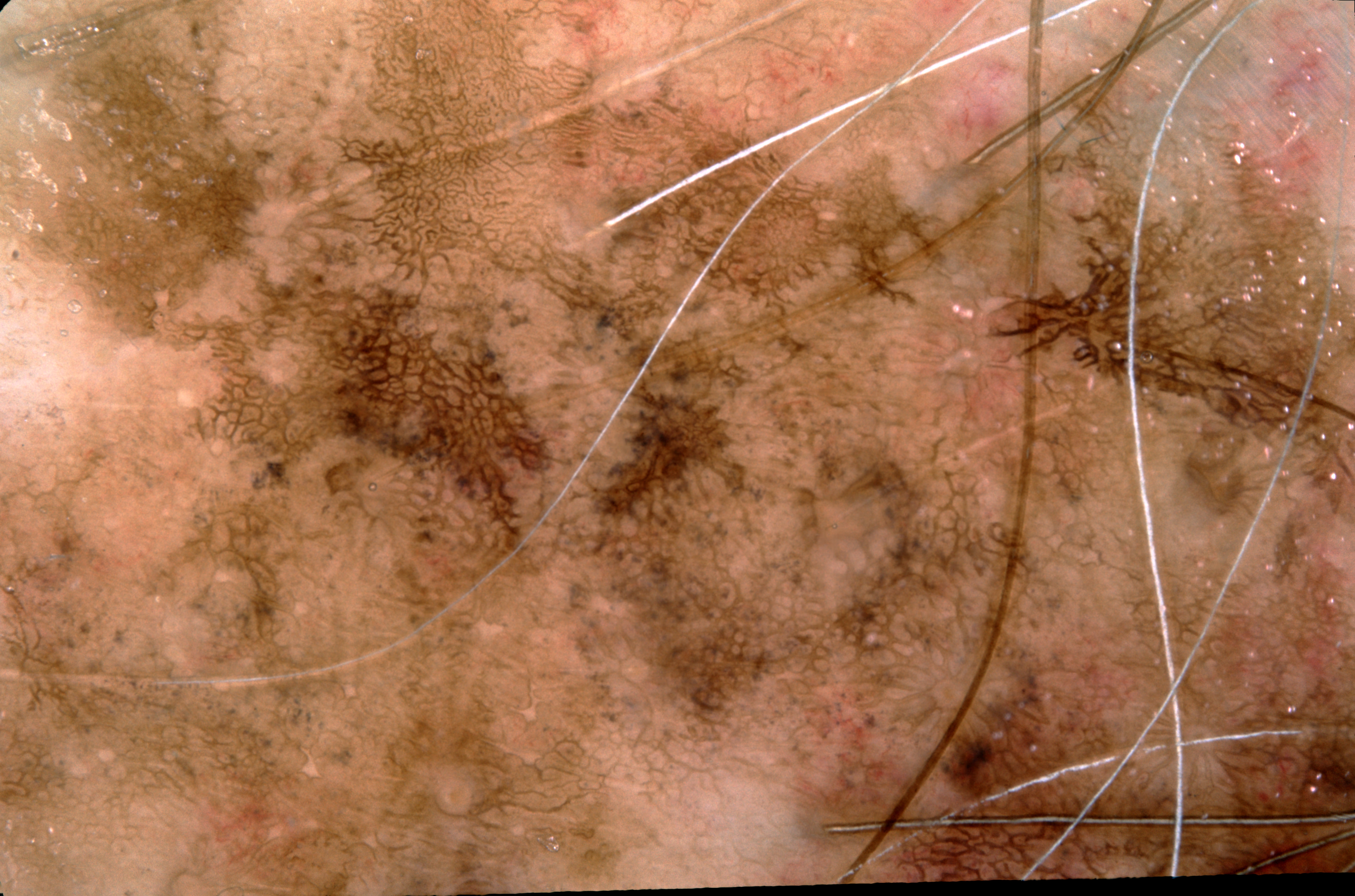A male subject, aged 68 to 72. A dermoscopy image of a single skin lesion. Dermoscopic review identifies pigment network, with no milia-like cysts, negative network, or streaks. The lesion reaches across nearly the entire image. The biopsy diagnosis was a melanoma.